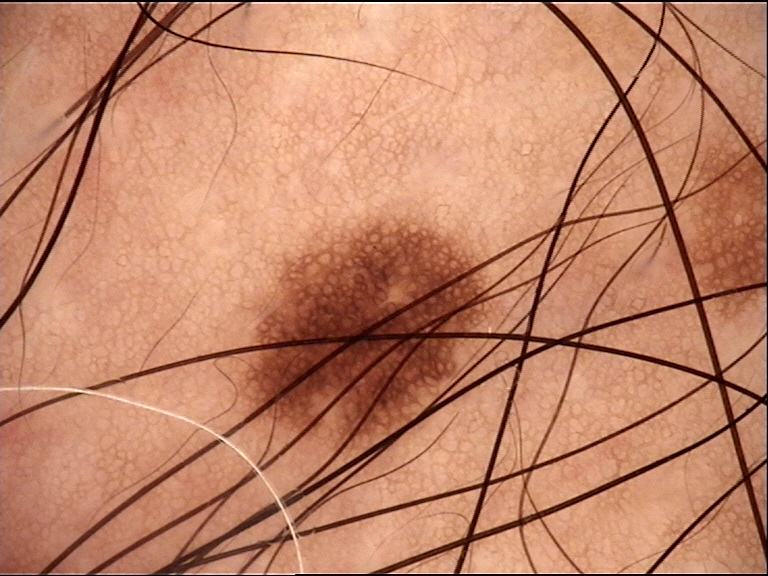The diagnosis was a junctional nevus.